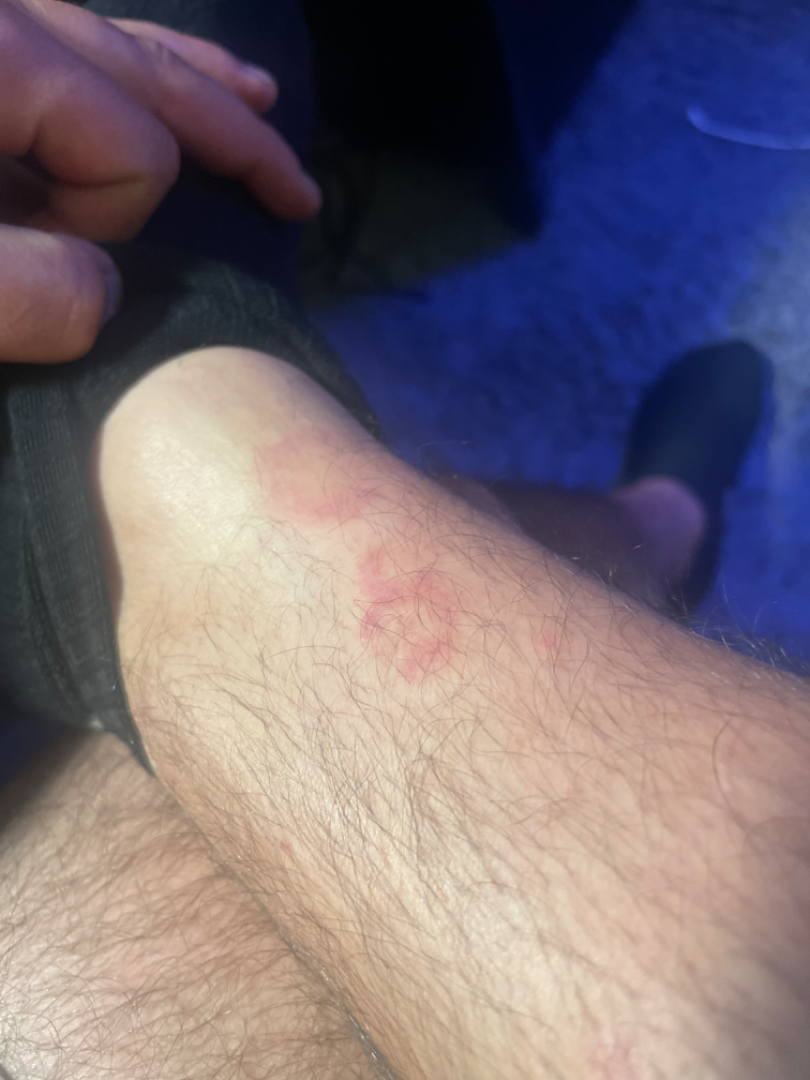| feature | finding |
|---|---|
| assessment | ungradable on photographic review |
| contributor | male |
| lesion symptoms | none reported |
| patient's own categorization | a rash |
| symptom duration | about one day |
| image framing | at an angle |
| site | leg |